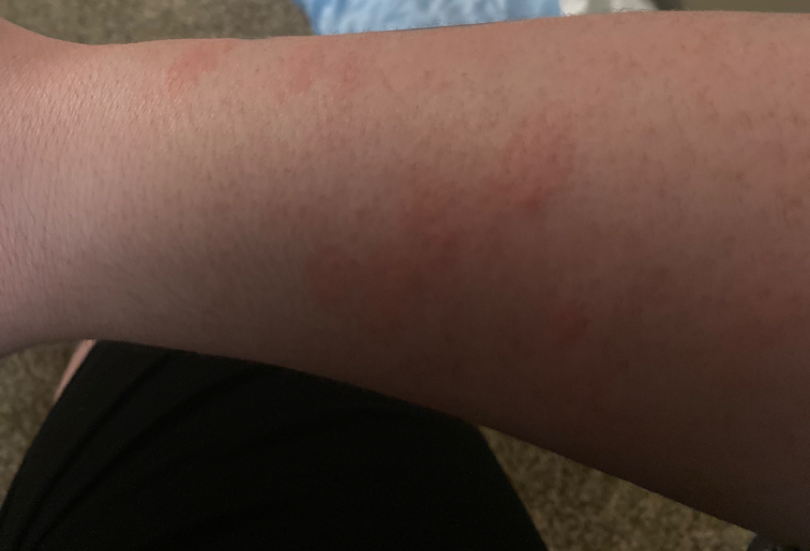{"skin_tone": {"fitzpatrick": "III"}, "shot_type": "at an angle", "body_site": "arm", "texture": ["flat", "raised or bumpy"], "patient_category": "a rash", "duration": "less than one week", "differential": {"leading": ["Urticaria"], "considered": ["Eczema"]}}